A dermoscopic image of a skin lesion.
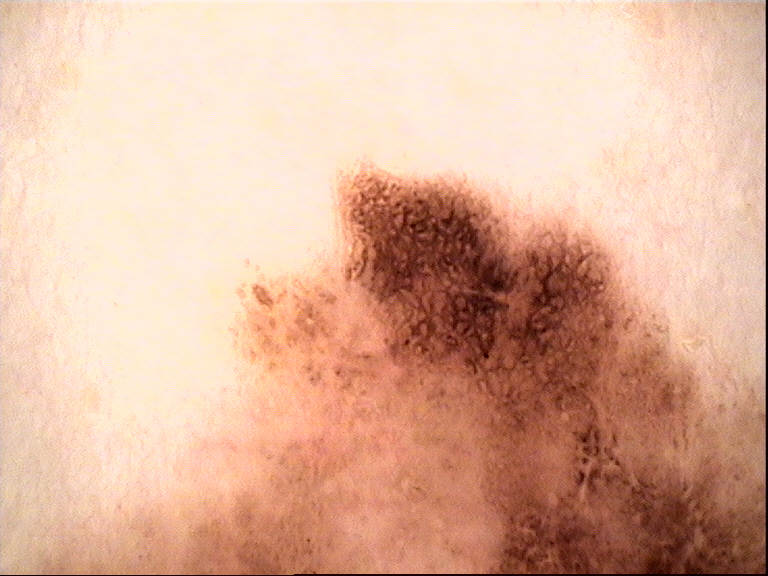Biopsy-confirmed as an acral lentiginous melanoma.